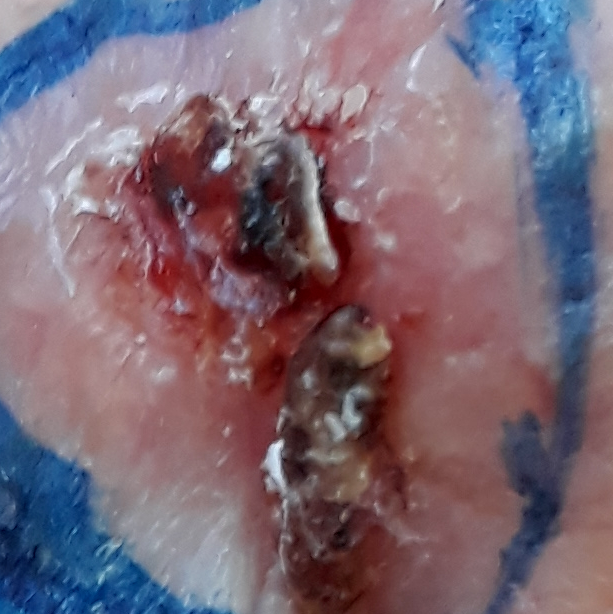* exposures · tobacco use, prior malignancy (patient or family)
* Fitzpatrick · II
* patient · female, in their 80s
* lesion diameter · approx. 13 × 3 mm
* diagnostic label · basal cell carcinoma (biopsy-proven)